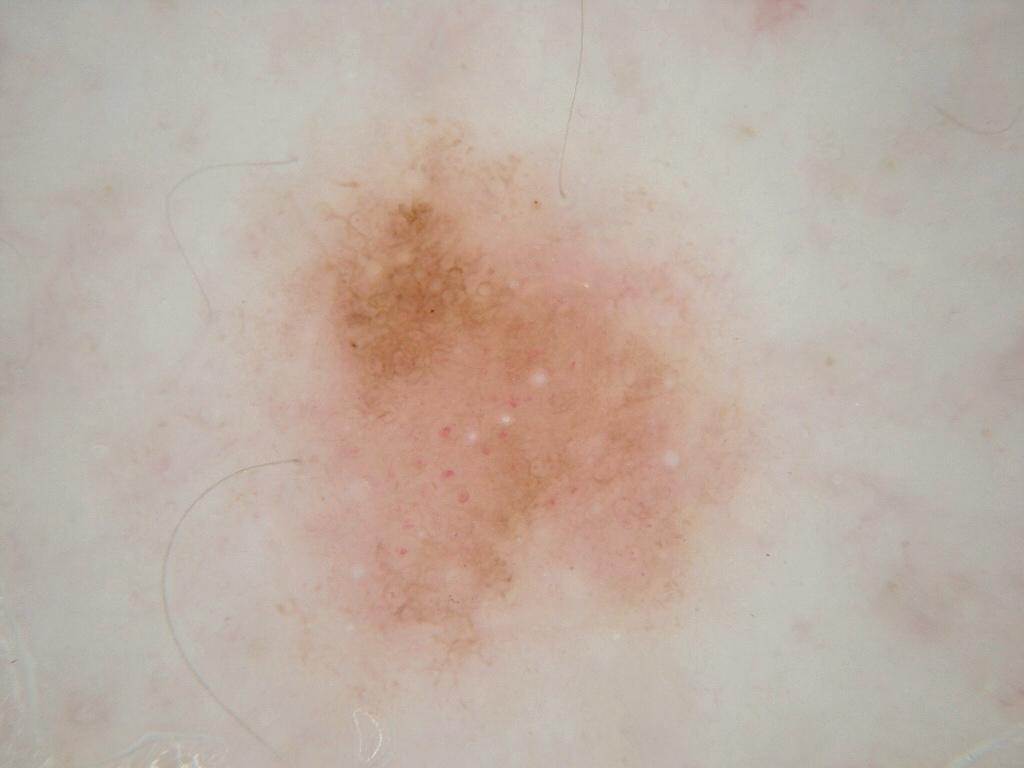Findings: A dermoscopic close-up of a skin lesion. With coordinates (x1, y1, x2, y2), the lesion's extent is [221, 98, 787, 721]. A large lesion occupying much of the field. Dermoscopically, the lesion shows milia-like cysts and pigment network; no globules, negative network, or streaks. Conclusion: The clinical diagnosis was a melanocytic nevus, a benign skin lesion.